The lesion involves the arm; this image was taken at an angle:
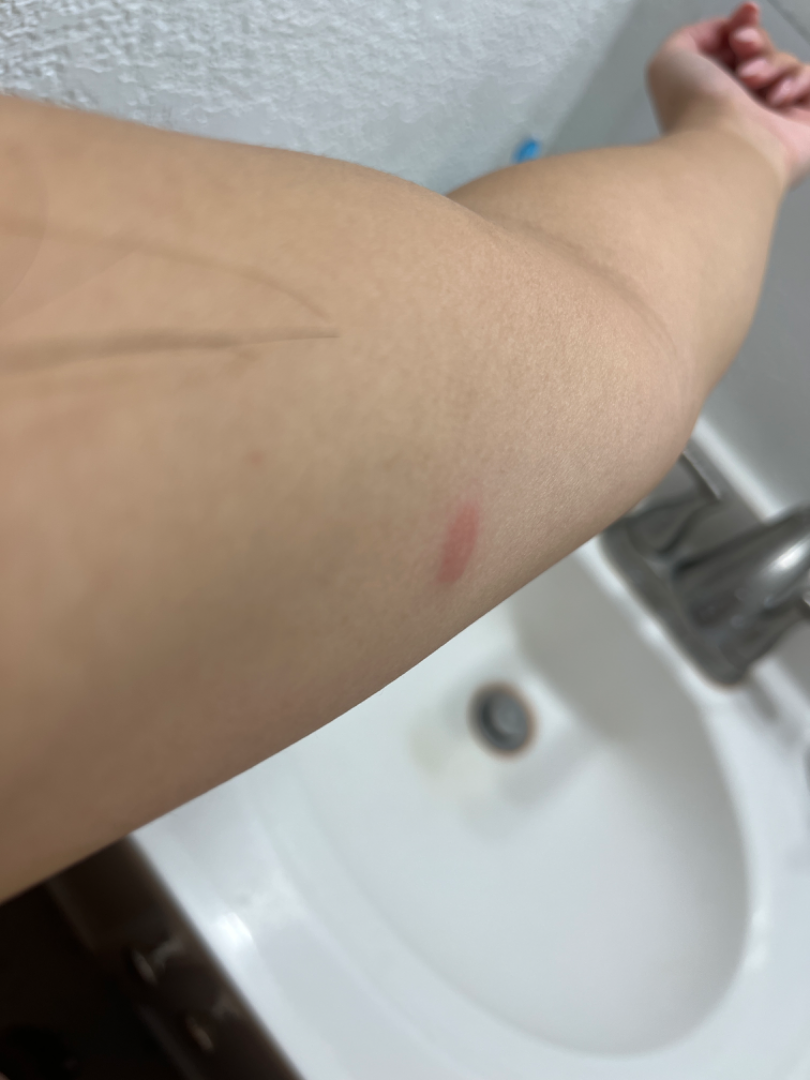Q: Patient's own categorization?
A: skin that appeared healthy to them
Q: How does the lesion feel?
A: raised or bumpy
Q: How long has this been present?
A: about one day
Q: What conditions are considered?
A: Insect Bite and Mastocytoma were considered with similar weight